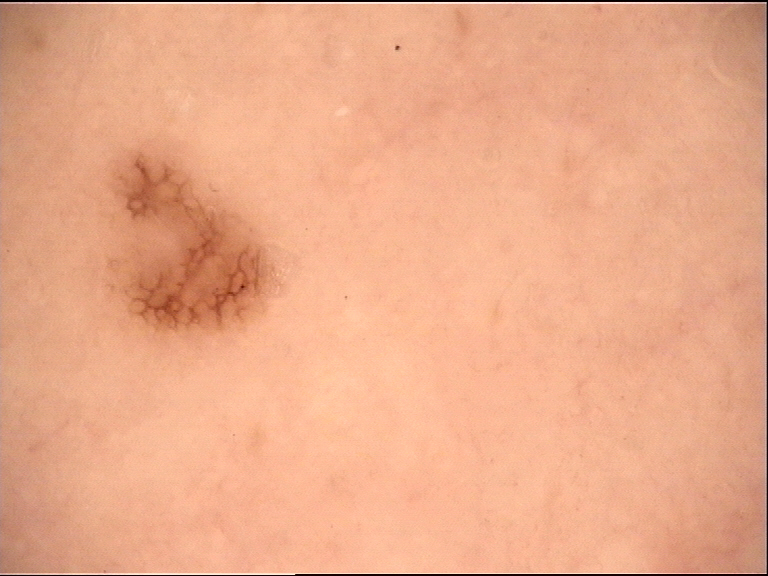A dermoscopy image of a single skin lesion.
Diagnosed as a dysplastic junctional nevus.